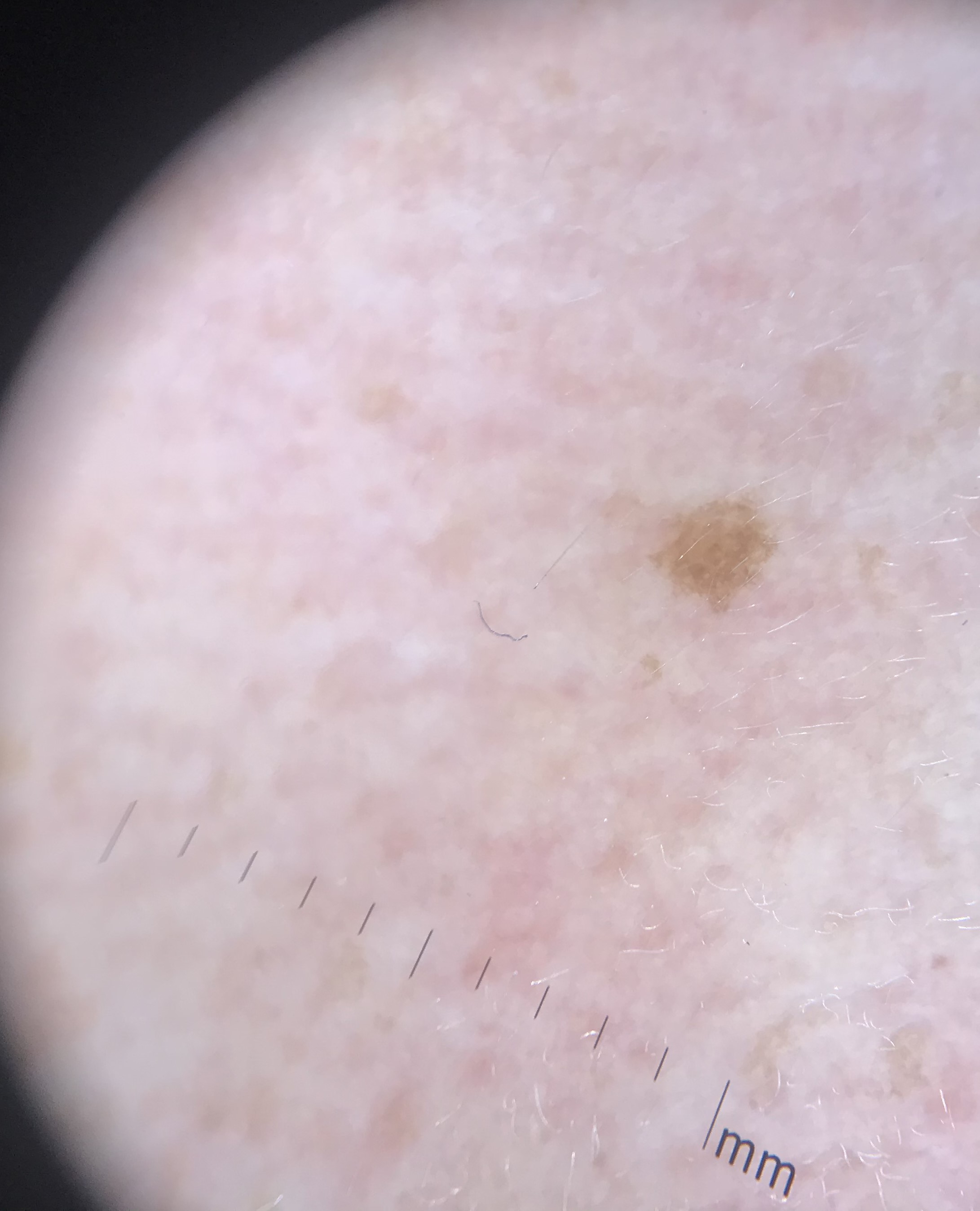A dermoscopy image of a single skin lesion.
Classified as a keratinocytic, benign lesion — a seborrheic keratosis.